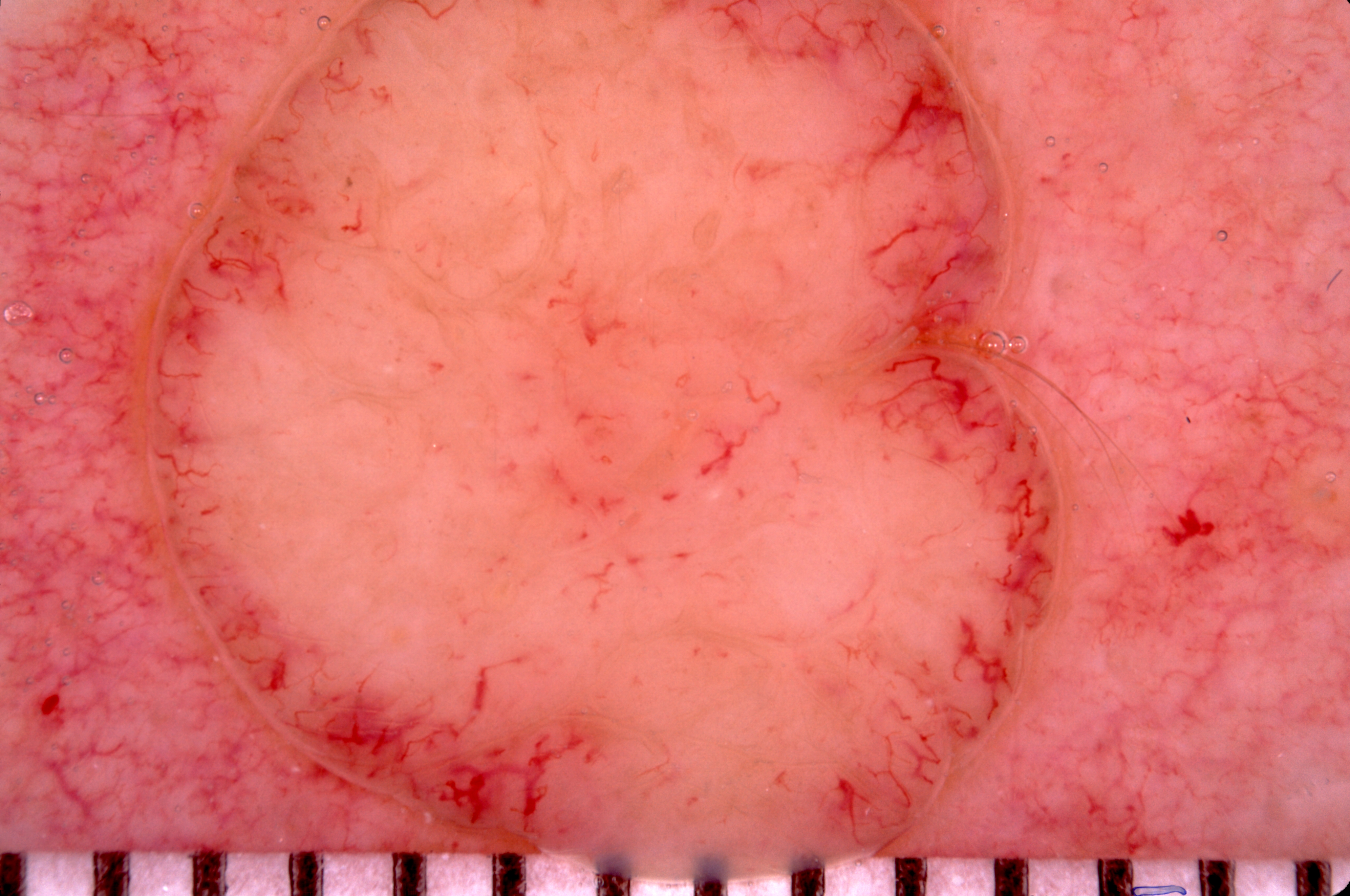A skin lesion imaged with a dermatoscope. The lesion runs off the edge of the field of view. A prominent lesion filling much of the field. The lesion is located at x1=127 y1=0 x2=1074 y2=890. Dermoscopic examination shows milia-like cysts; no negative network, pigment network, or streaks. Clinically diagnosed as a melanocytic nevus, a benign lesion.